The patient is male · the lesion involves the leg · close-up view — 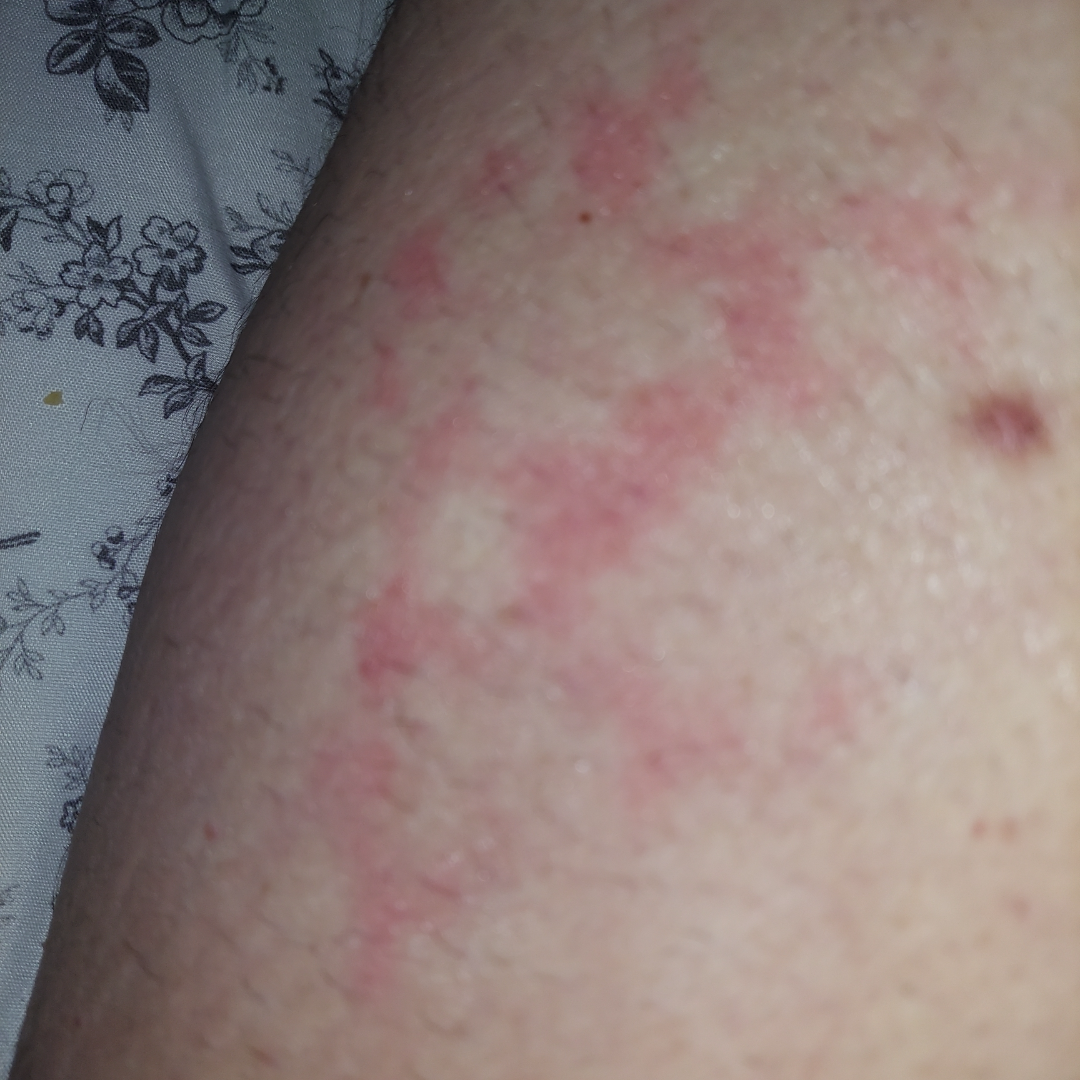No differential diagnosis could be assigned on photographic review. Self-categorized by the patient as a rash. Texture is reported as flat. The patient reported no relevant symptoms from the lesion. The patient reported no systemic symptoms.